A close-up photograph.
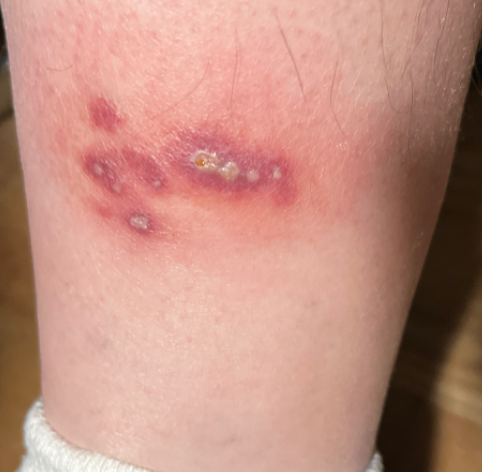Impression: The favored diagnosis is Insect Bite; with consideration of Pyoderma Gangrenosum; possibly purulent pustules.